This image was taken at an angle. The contributor is 18–29, female. The arm, top or side of the foot and back of the torso are involved: 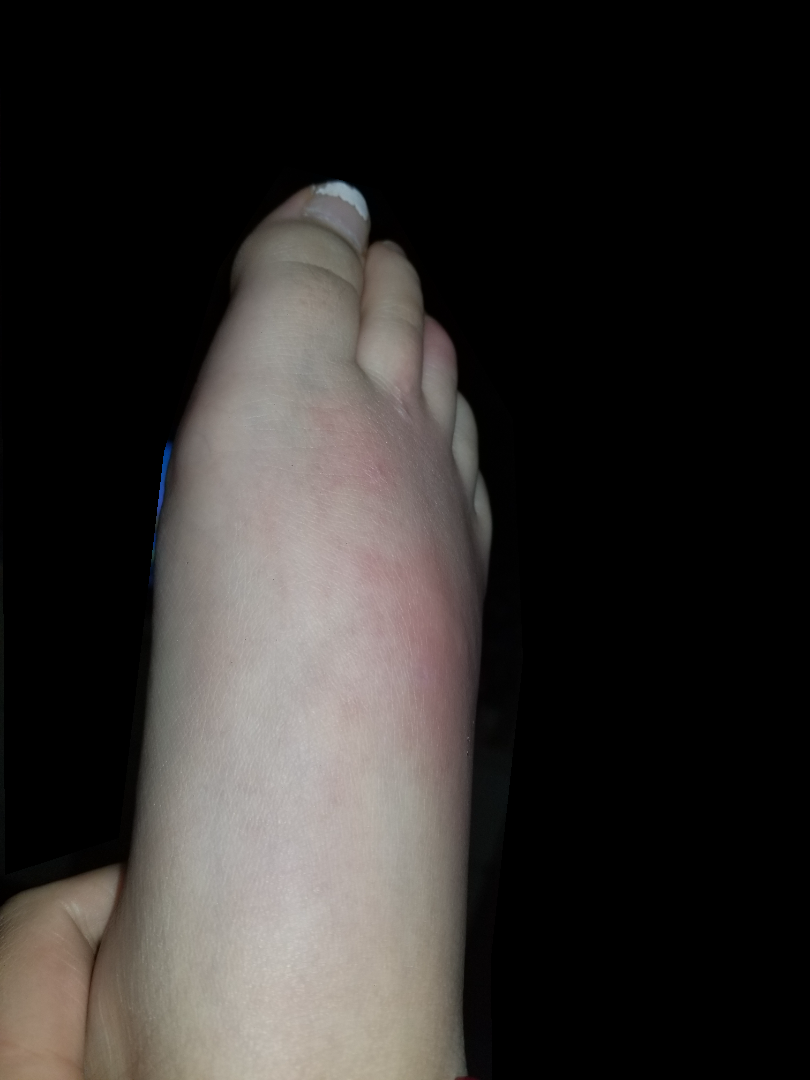differential: most consistent with Urticaria; with consideration of Superficial frostbite; an alternative is Insect Bite; less probable is Eczema